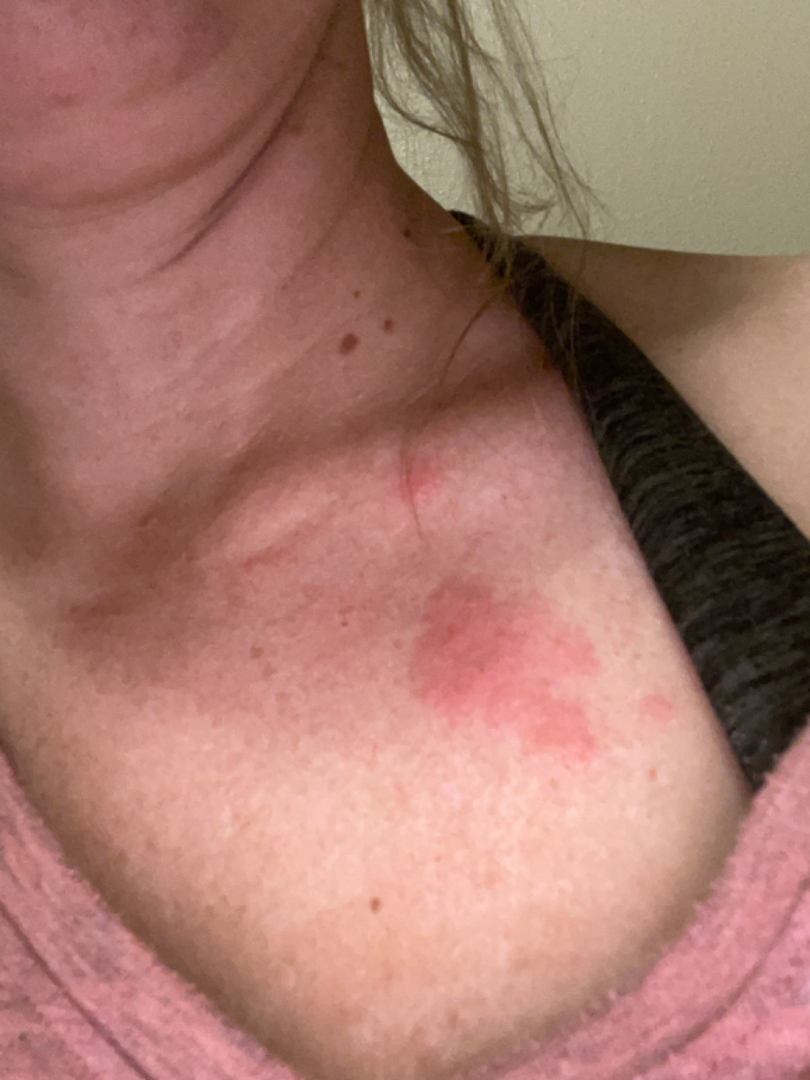Clinical context:
The photograph is a close-up of the affected area.
Assessment:
Most likely Insect Bite.